Acquired for a research image collection, with no referral diagnosis · a female subject 55 years old · a macroscopic clinical photograph of a skin lesion: 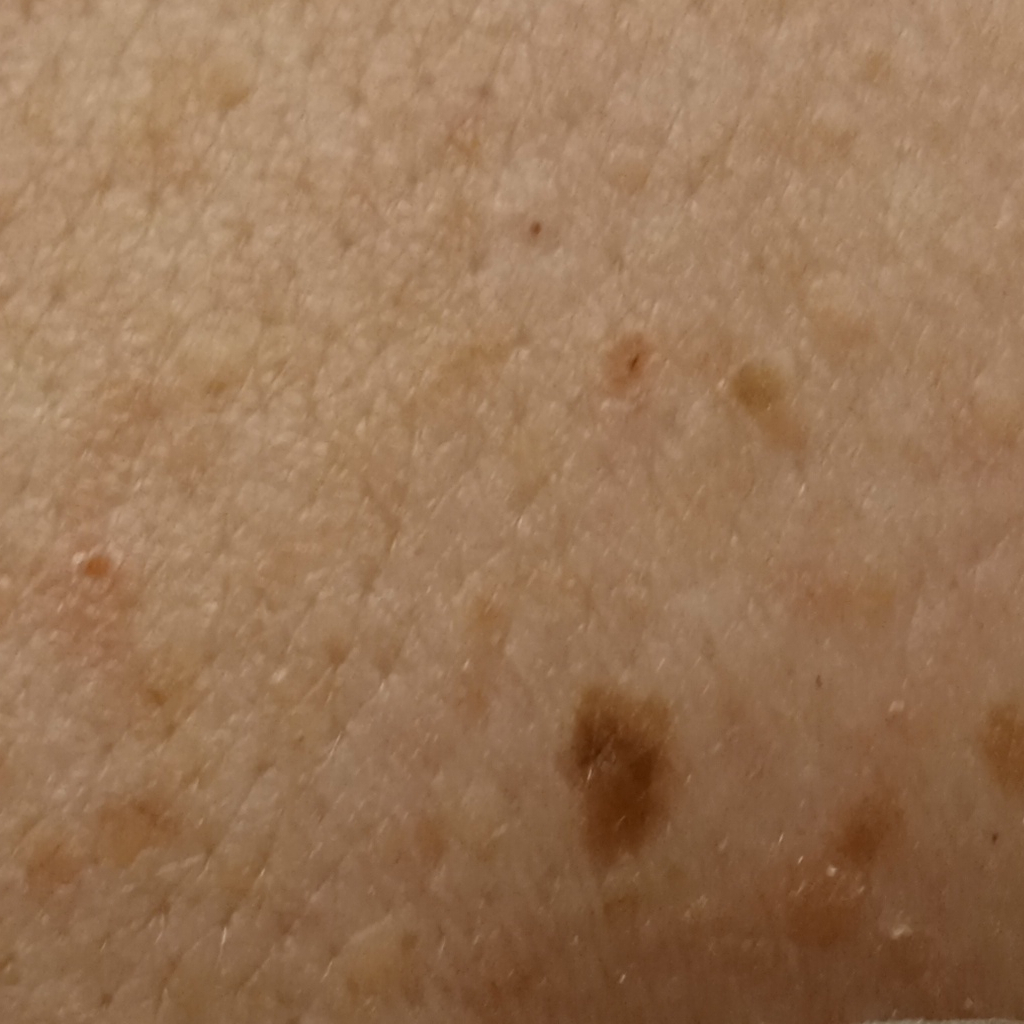The lesion is located on the back. Dermatologist review favored a melanocytic nevus.